Female patient, age 30–39; close-up view; the affected area is the arm; self-categorized by the patient as a rash; the contributor notes itching; the condition has been present for less than one week:
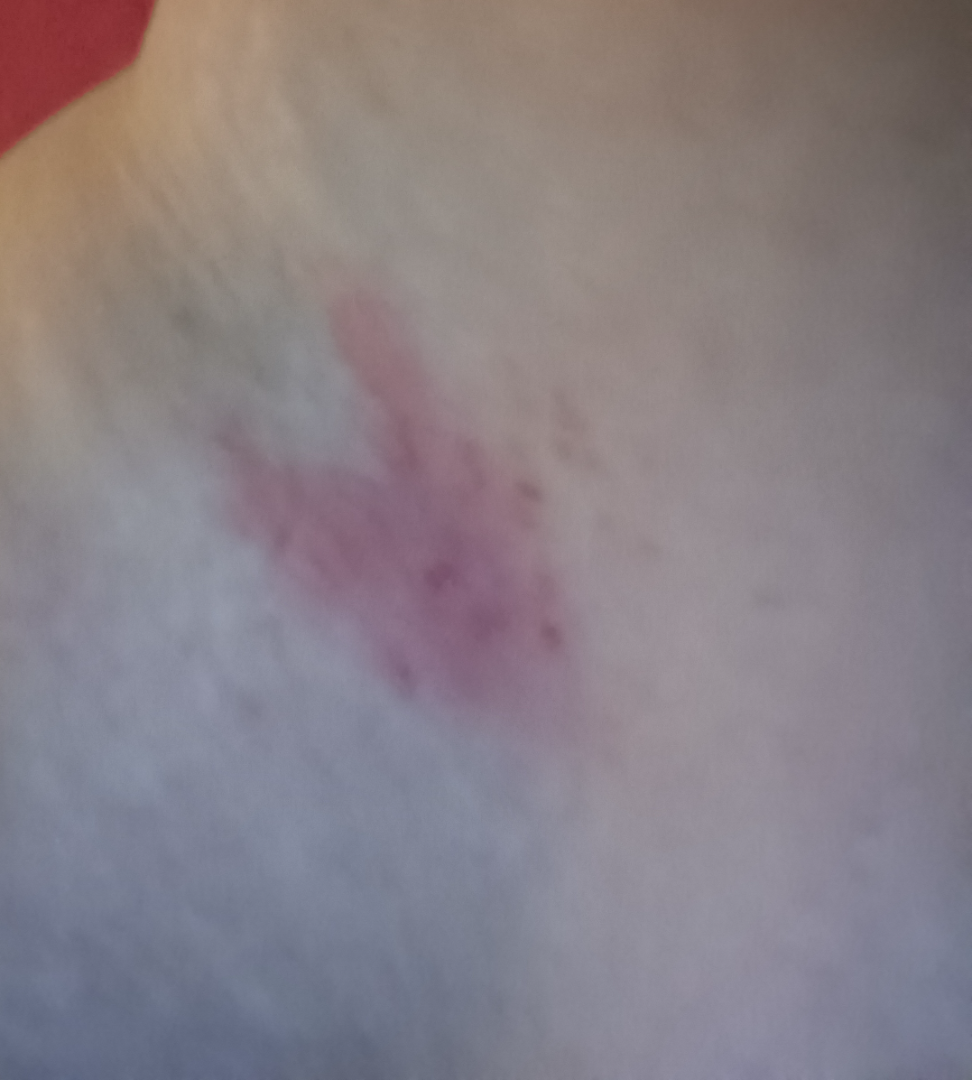assessment: unable to determine.